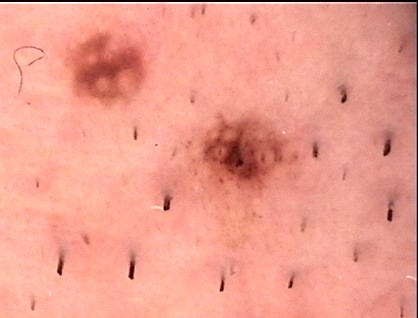A skin lesion imaged with a dermatoscope. The morphology is that of a compound, banal lesion. Consistent with a Miescher nevus.